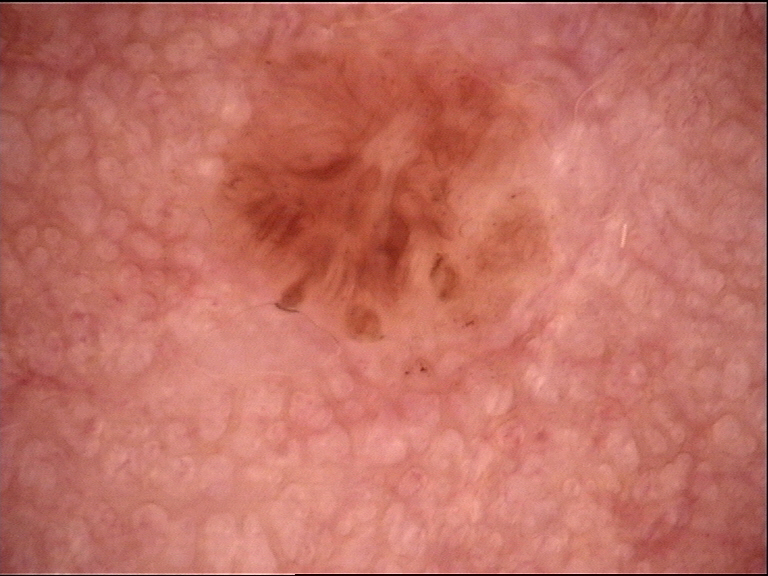Labeled as a dermal nevus.